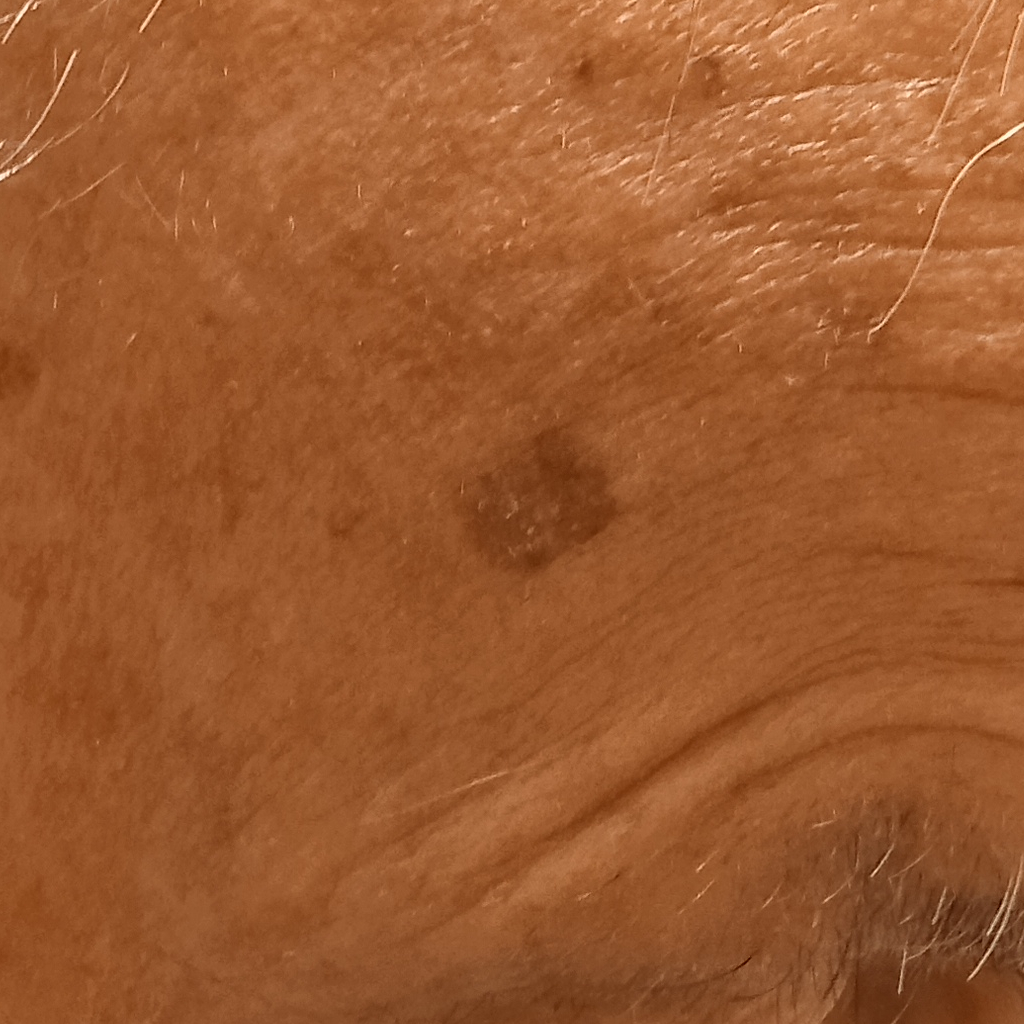<skin_lesion>
<sun_reaction>skin reddens with sun exposure</sun_reaction>
<risk_factors>
<positive>a personal history of cancer, a personal history of skin cancer</positive>
</risk_factors>
<mole_burden>few melanocytic nevi overall</mole_burden>
<image>clinical photo</image>
<lesion_location>the face</lesion_location>
<lesion_size>
<diameter_mm>8.7</diameter_mm>
</lesion_size>
<diagnosis>
<name>basal cell carcinoma</name>
<malignancy>malignant</malignancy>
<procedure>excision</procedure>
<tumor_thickness_mm>2.5</tumor_thickness_mm>
</diagnosis>
</skin_lesion>